Numerous moles by the patient's own estimate · the patient says their skin reddens painfully with sun exposure · on a questionnaire the patient reported a family history of skin cancer, a personal history of skin cancer, and immunosuppression.
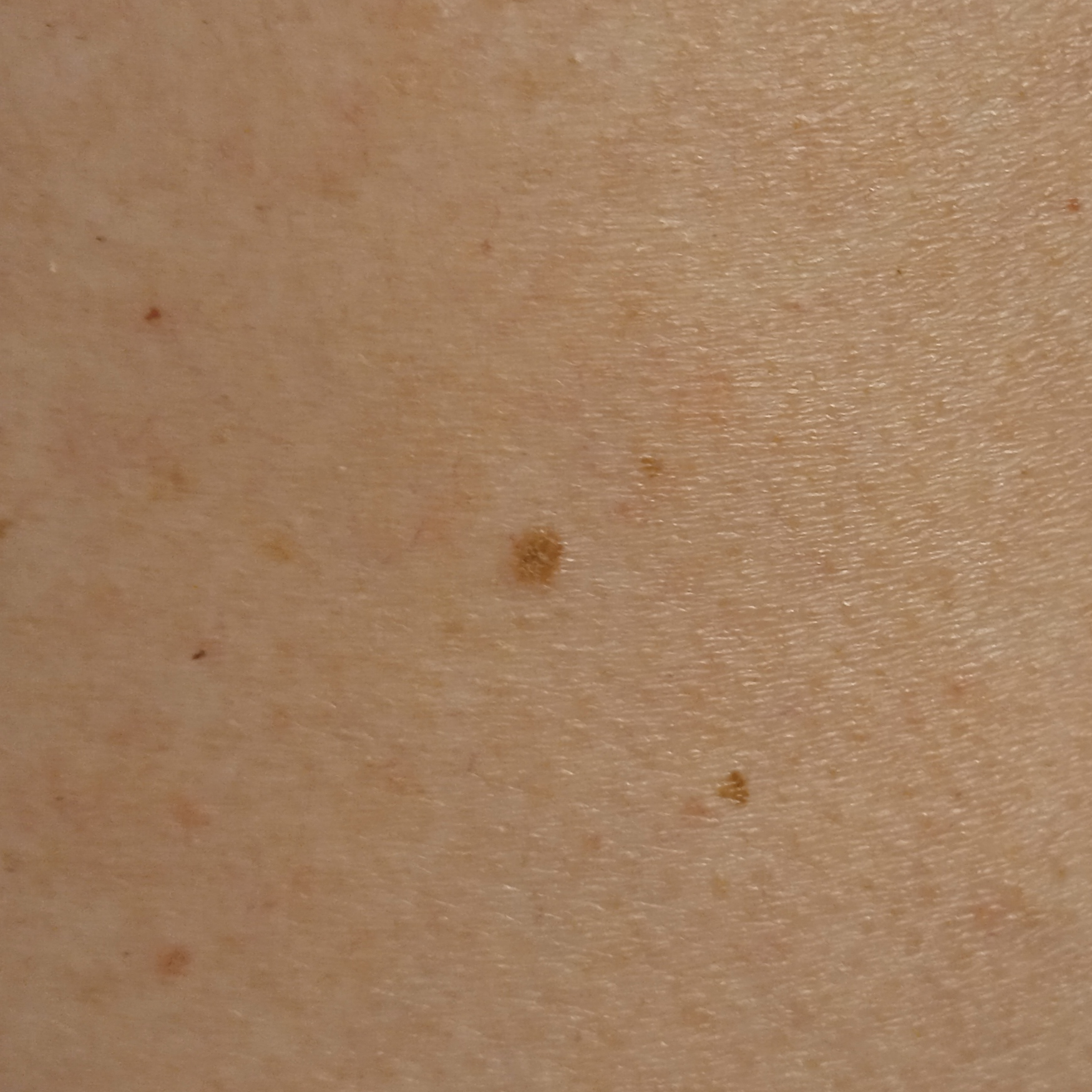lesion size: 3.3 mm; assessment: seborrheic keratosis (dermatologist consensus).